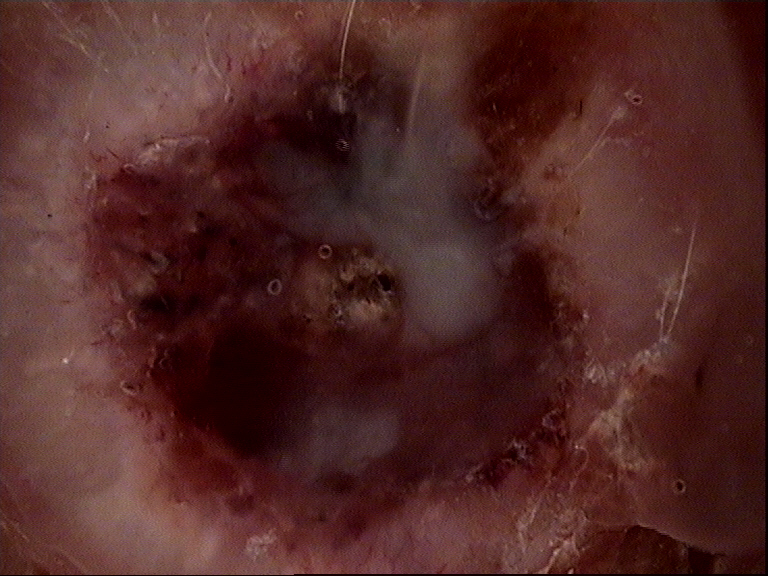Summary: Dermoscopy of a skin lesion. Diagnosis: Histopathologically confirmed as a melanoma.